A dermoscopic image of a skin lesion:
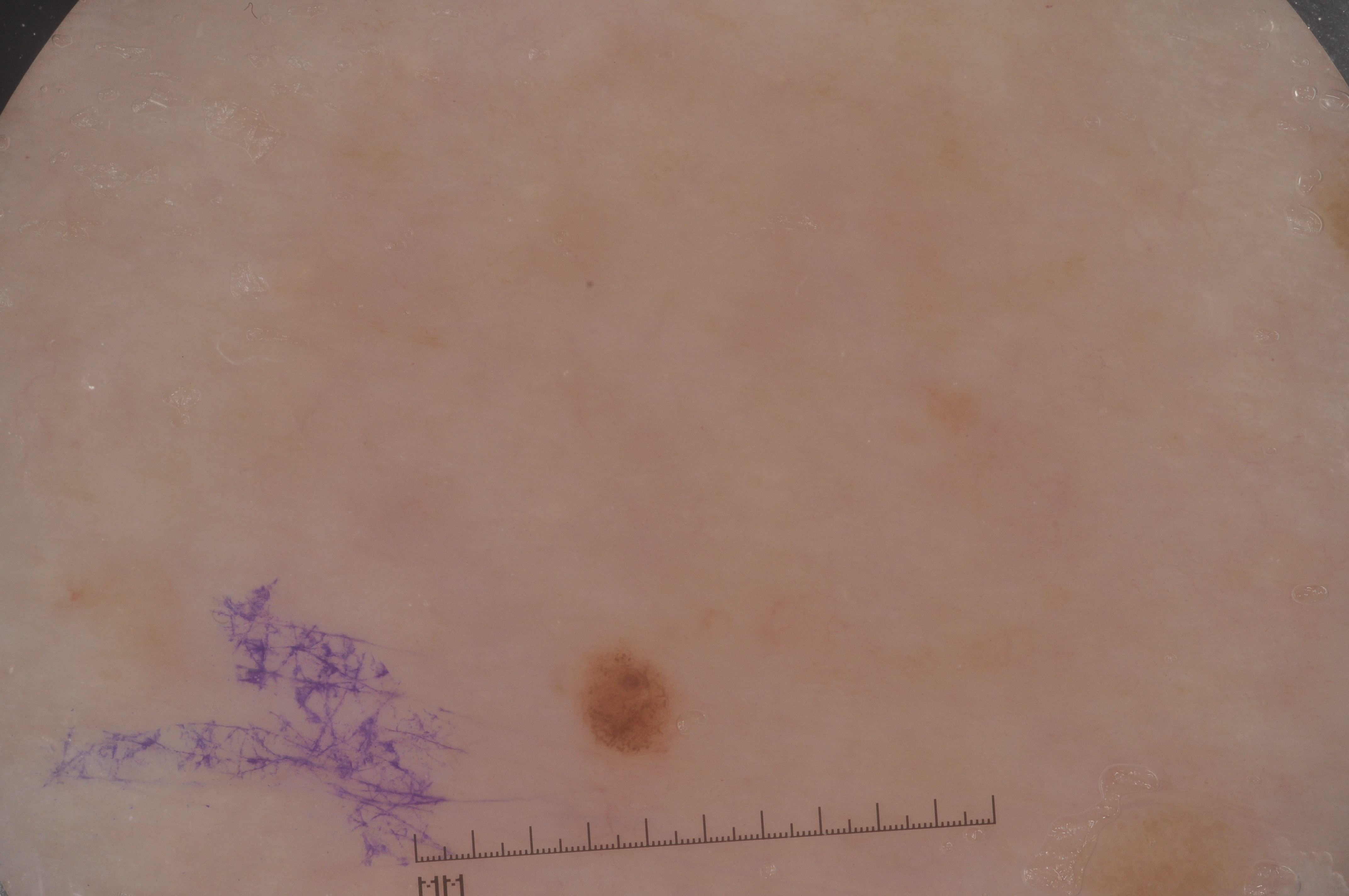The dermoscopic pattern shows pigment network. A small lesion occupying a minor part of the field. With coordinates (x1, y1, x2, y2), the visible lesion spans [580,646,679,757]. Consistent with a melanocytic nevus, a benign lesion.